The photo was captured at an angle · skin tone: Fitzpatrick II: 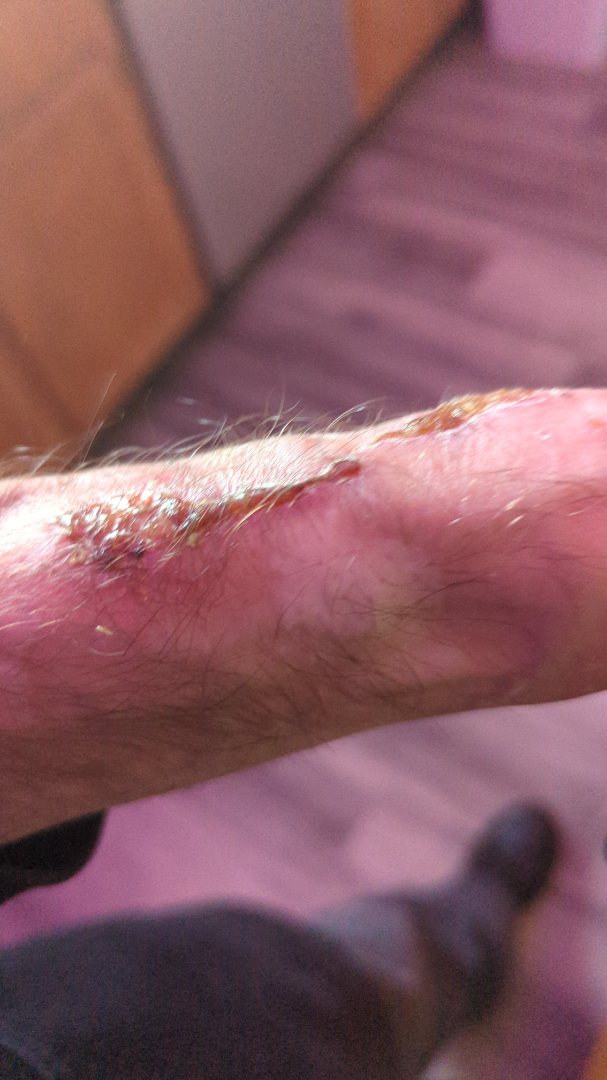Review: On photographic review, the leading consideration is Impetigo; also consider Bullous Pemphigoid.